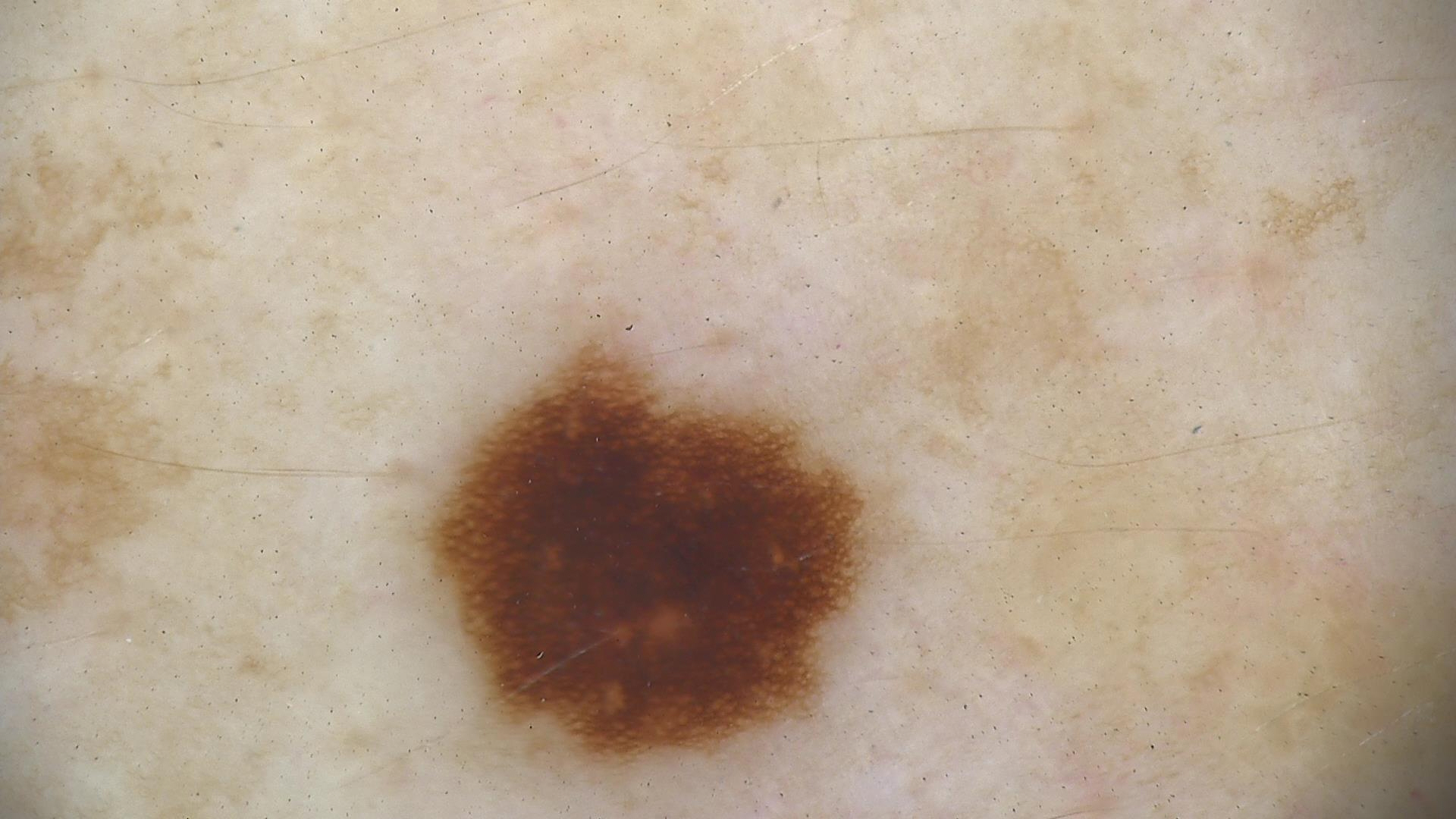Case:
- modality: dermoscopy
- assessment: dysplastic junctional nevus (expert consensus)